This is a close-up image: 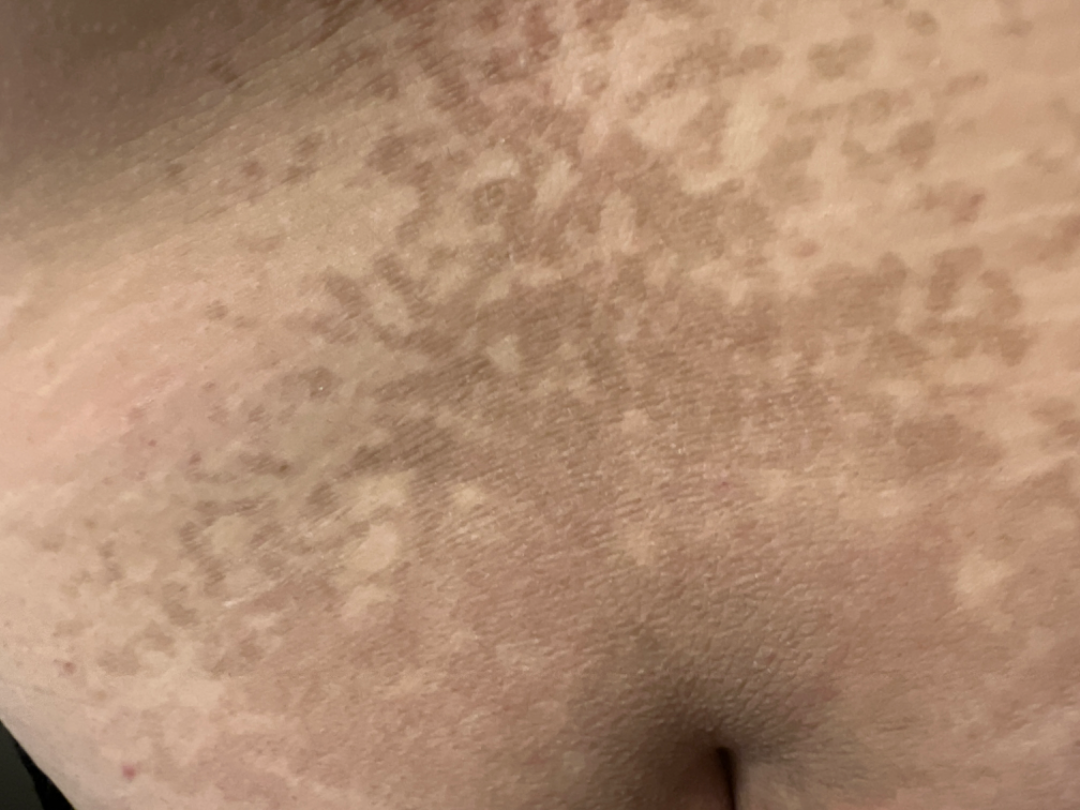differential = single-reviewer assessment: favoring Confluent and reticulate papillomatosis; with consideration of Erythema ab igne; an alternative is Tinea Versicolor.